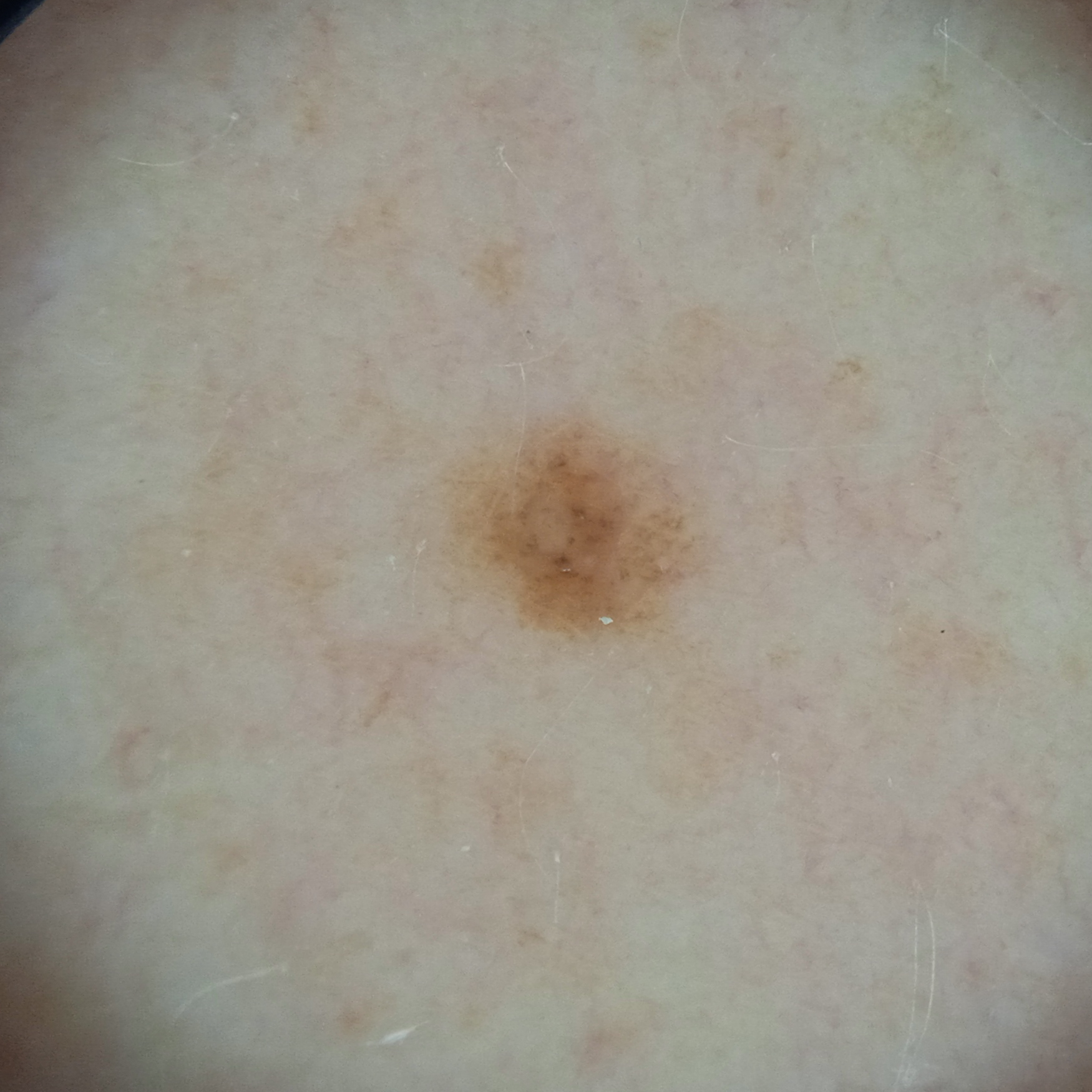The patient says their skin reddens painfully with sun exposure. A female subject 48 years old. Acquired for a research image collection, with no referral diagnosis. A dermoscopic image of a skin lesion. The patient describes having few moles overall. The patient reports a history of sunbed use and a family history of skin cancer. The lesion is located on an arm. The lesion is about 2.7 mm across. The dermatologists' assessment was a melanocytic nevus.